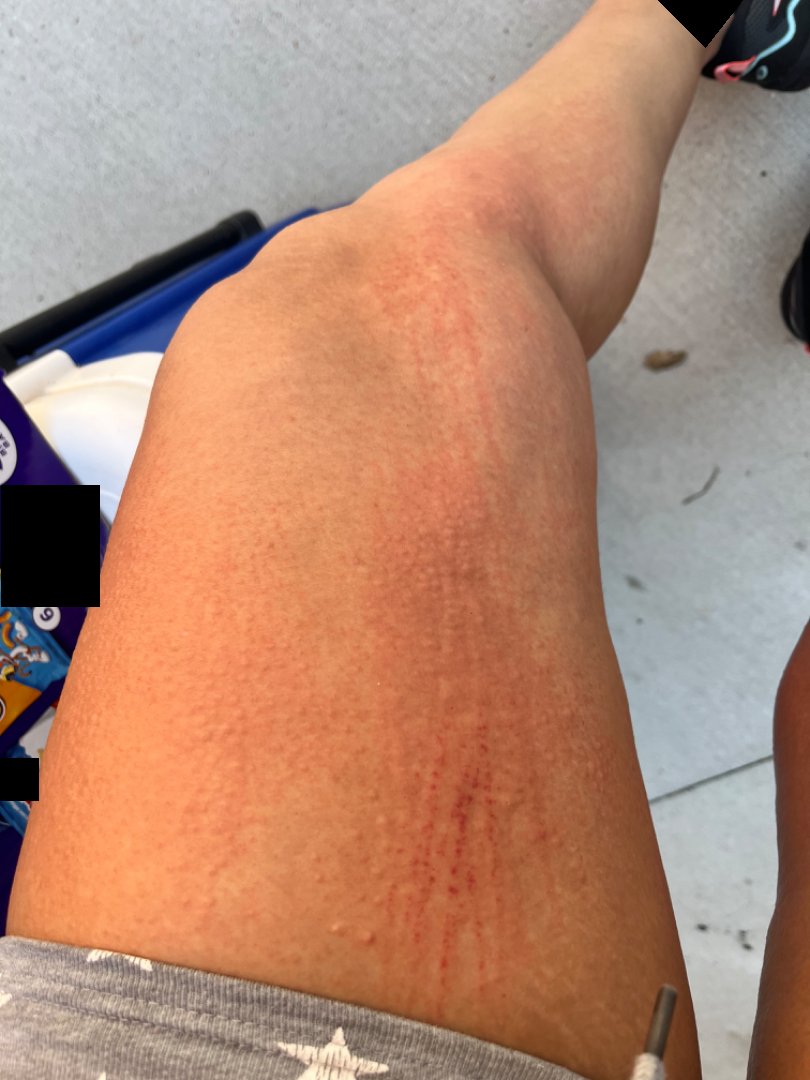Findings:
The skin findings could not be characterized from the image.
Background:
An image taken at an angle.